Dermoscopy of a skin lesion.
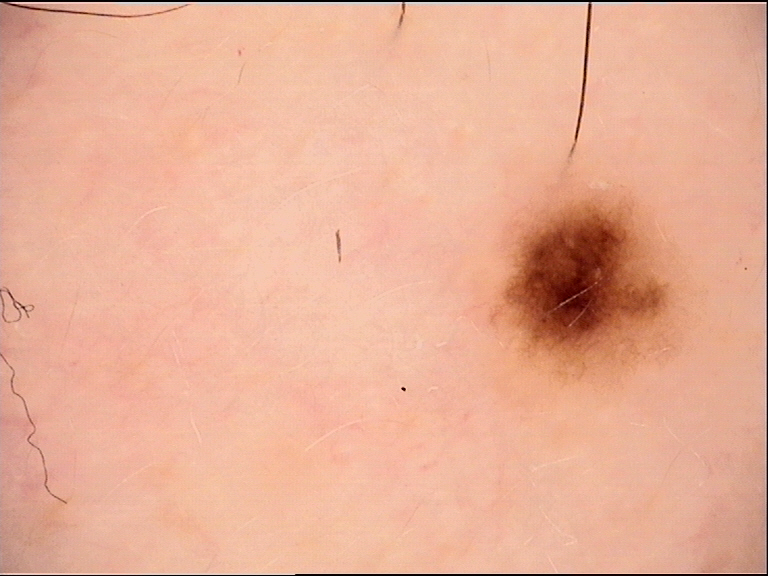Findings:
– diagnostic label — dysplastic junctional nevus (expert consensus)